Located on the back of the hand and palm; the photo was captured at a distance; the contributor is 60–69, female — 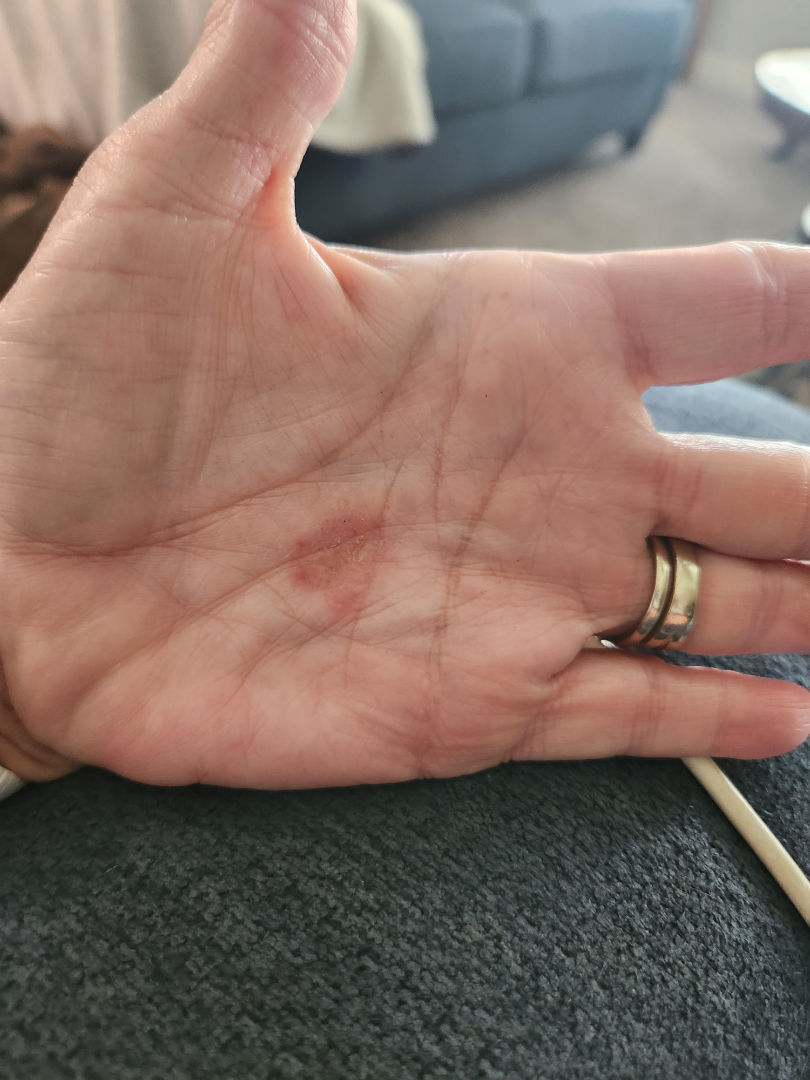Case summary:
* differential diagnosis · Psoriasis and Superficial wound of body region were considered with similar weight; less likely is Allergic Contact Dermatitis